A dermoscopic photograph of a skin lesion:
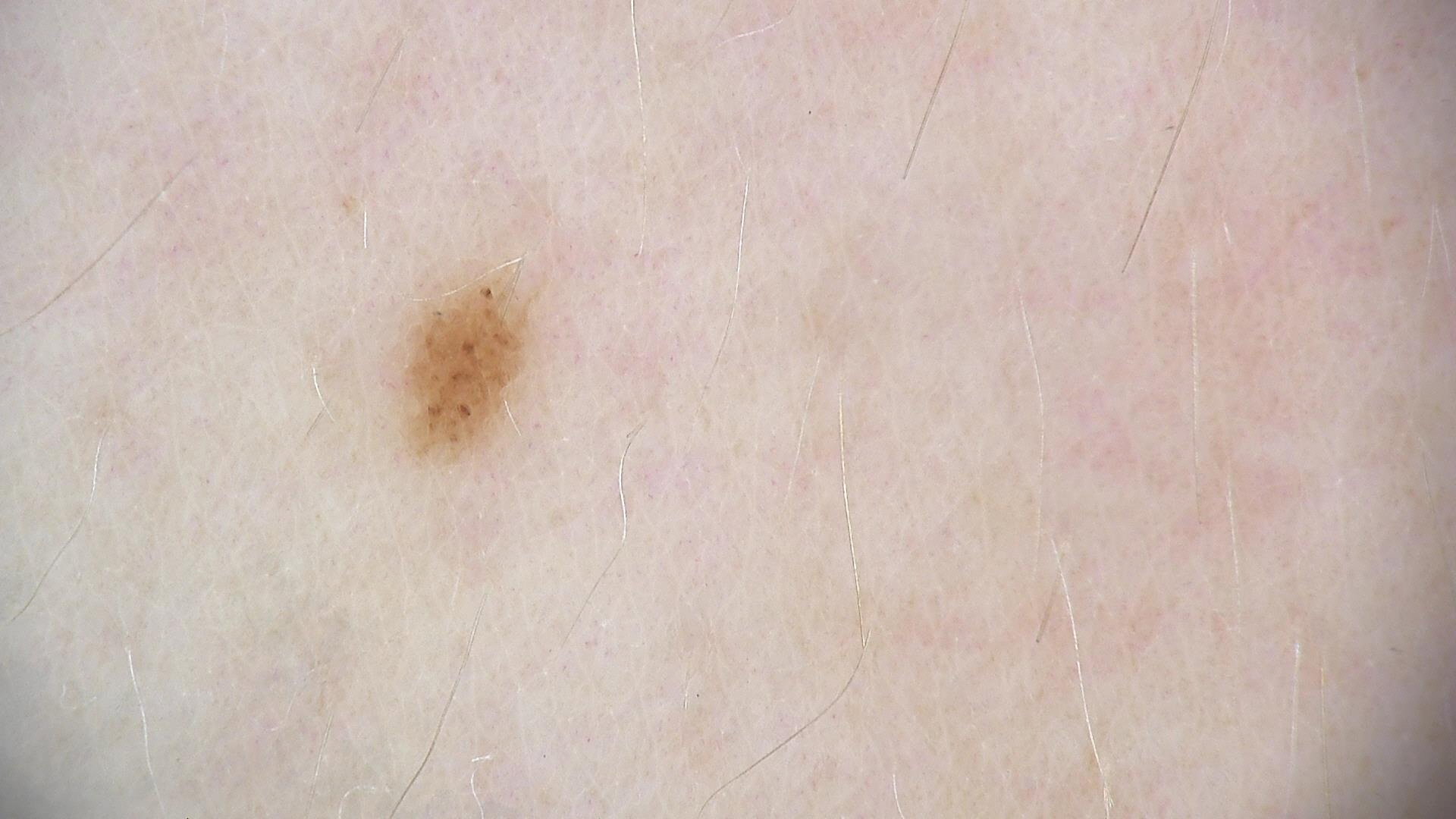class — compound nevus (expert consensus).